The patient describes having few moles overall · a male subject 81 years old · the patient reports a personal history of cancer and a family history of skin cancer.
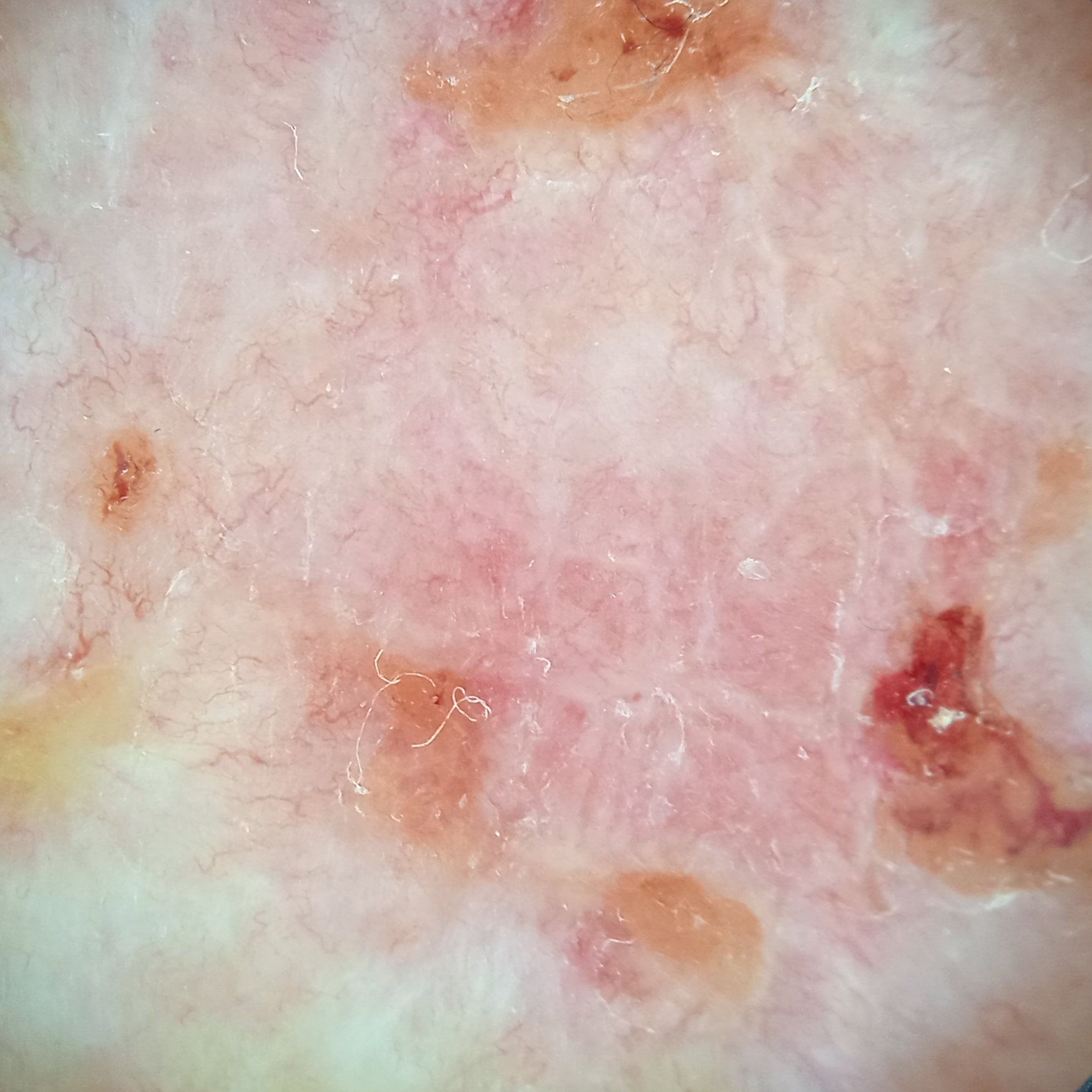<skin_lesion>
  <lesion_location>the back</lesion_location>
  <lesion_size>
    <diameter_mm>12.6</diameter_mm>
  </lesion_size>
  <diagnosis>
    <name>basal cell carcinoma</name>
    <malignancy>malignant</malignancy>
    <procedure>excision</procedure>
    <tumor_thickness_mm>3.0</tumor_thickness_mm>
  </diagnosis>
</skin_lesion>